A dermoscopic close-up of a skin lesion.
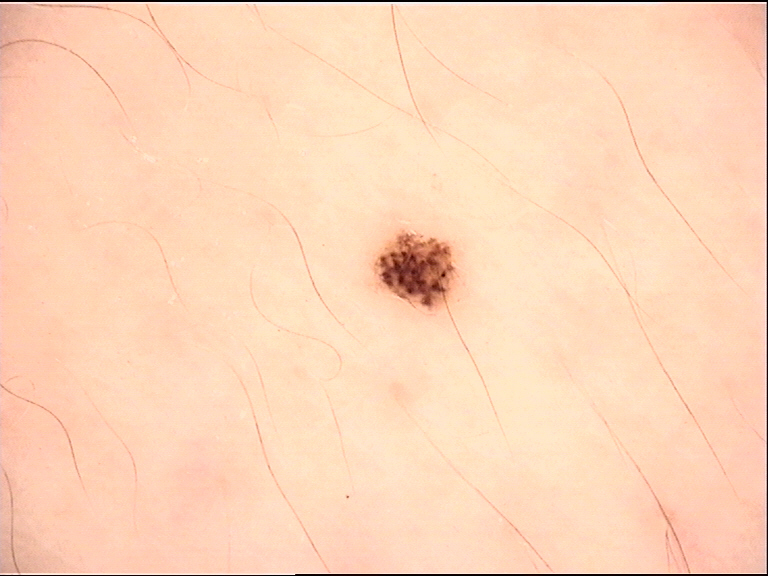Q: What was the diagnostic impression?
A: dysplastic junctional nevus (expert consensus)